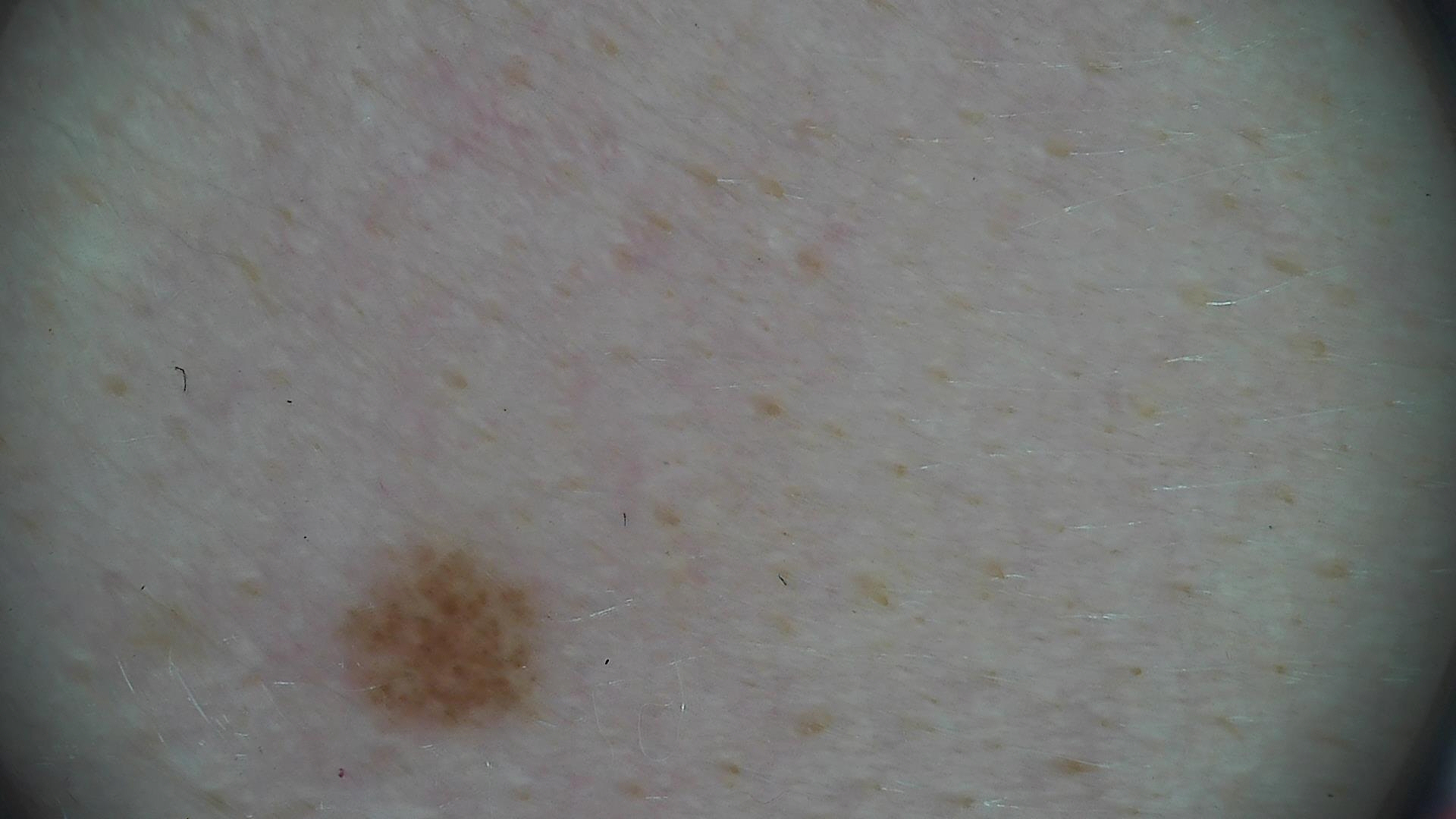The diagnostic label was a dysplastic junctional nevus.